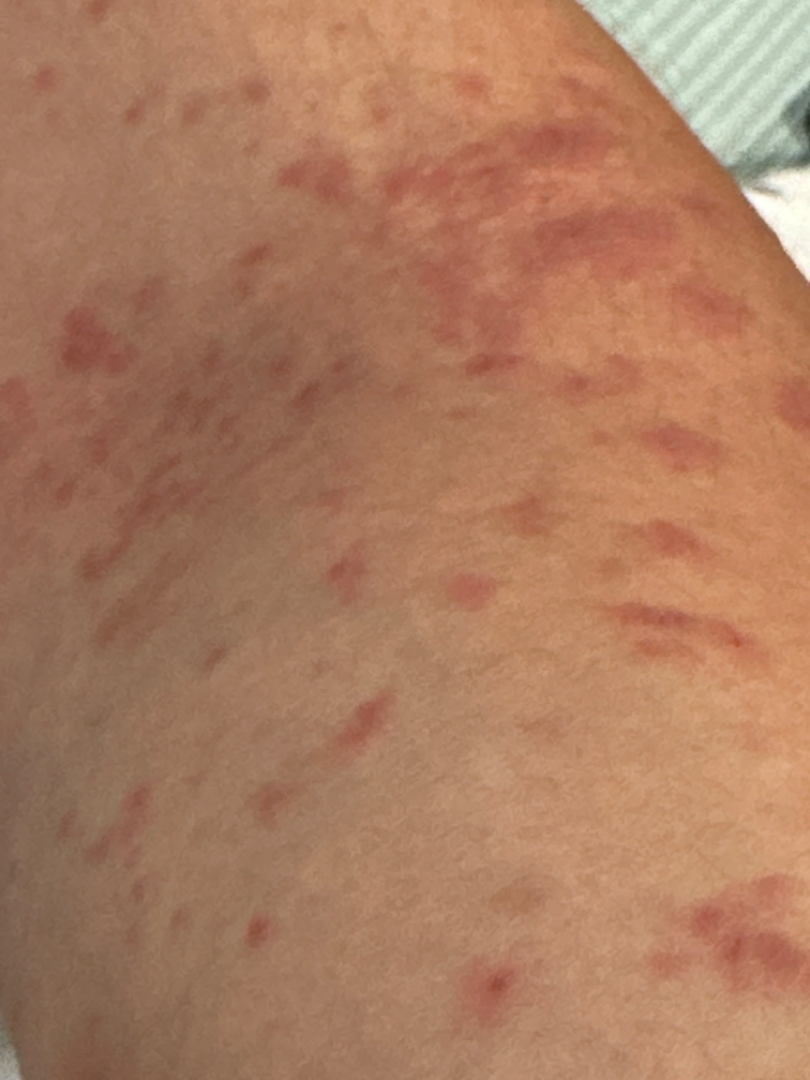This is a close-up image.
Reviewed remotely by one dermatologist: most consistent with Insect Bite; also on the differential is Allergic Contact Dermatitis.